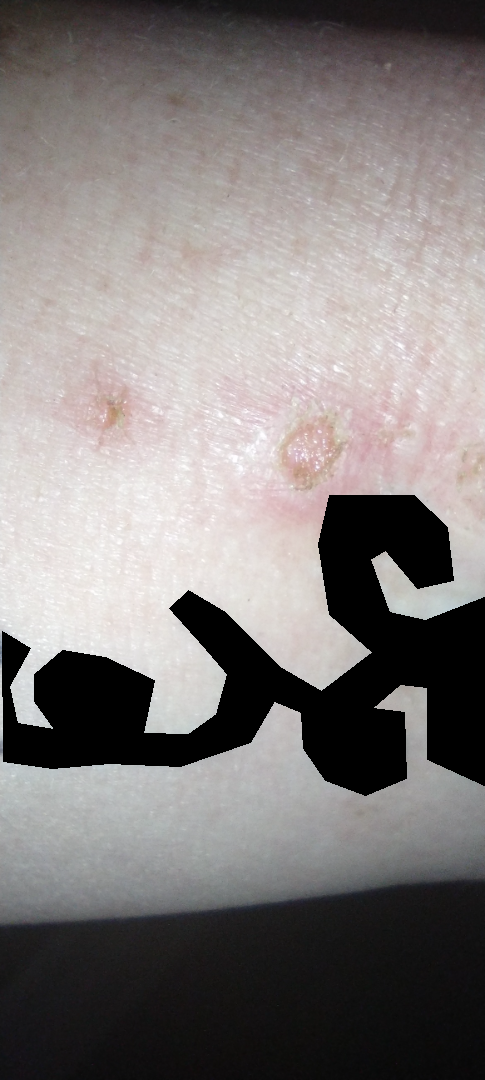Background: Close-up view. Located on the front of the torso, leg and arm. The subject is 40–49, female. Findings: Most likely Impetigo.